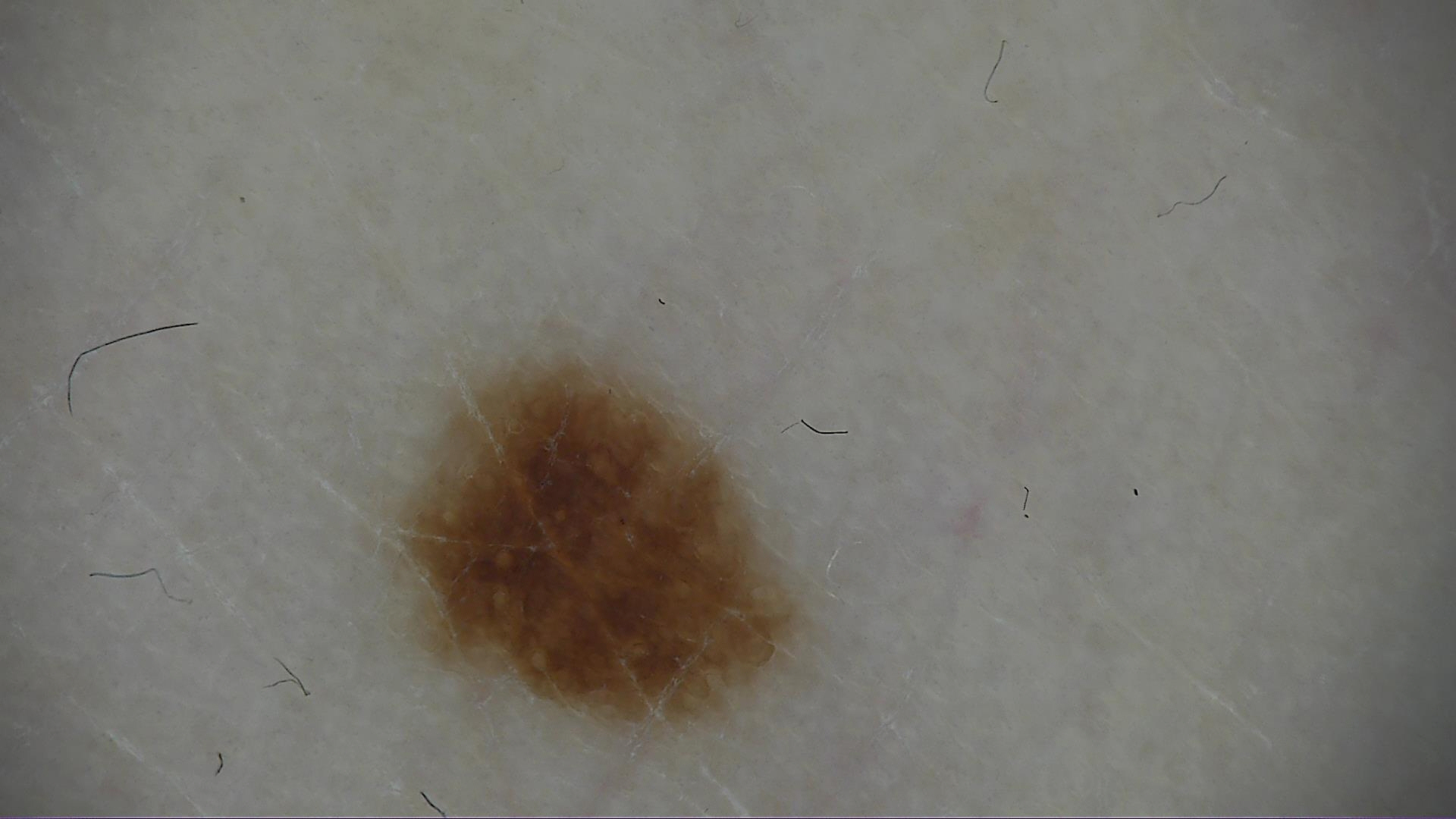The diagnostic label was a banal lesion — a junctional nevus.